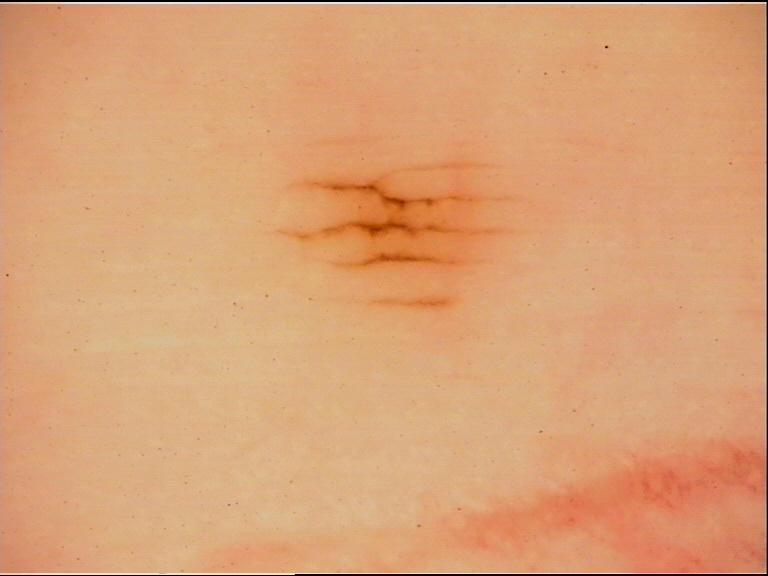A dermatoscopic image of a skin lesion.
The architecture is that of a banal lesion.
The diagnostic label was an acral junctional nevus.